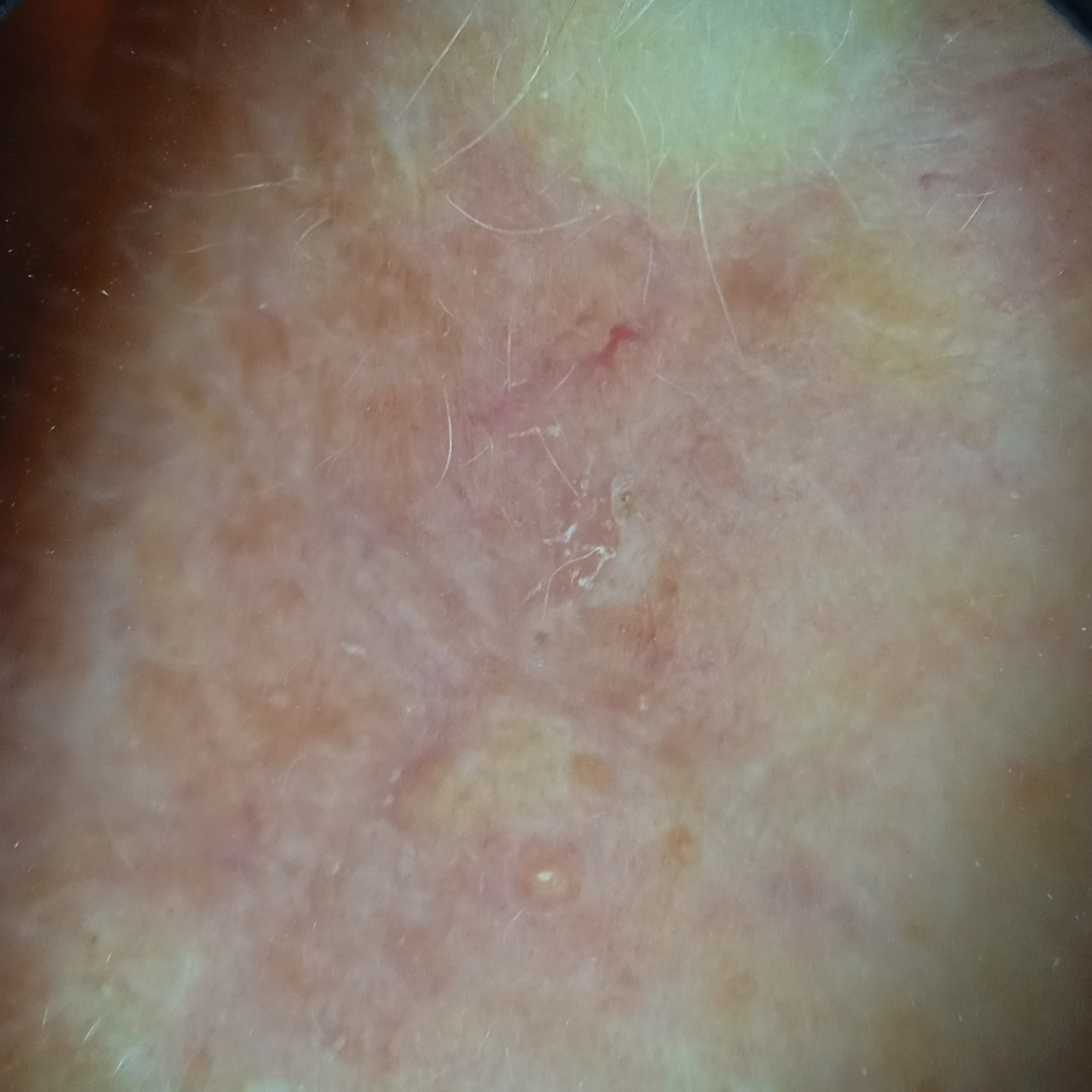sun reaction = skin tans without first burning; clinical context = research study (no referral diagnosis); relevant history = no personal history of cancer, no family history of skin cancer; nevus count = few melanocytic nevi overall; body site = the face; lesion size = 9.9 mm; assessment = actinic keratosis (dermatologist consensus).